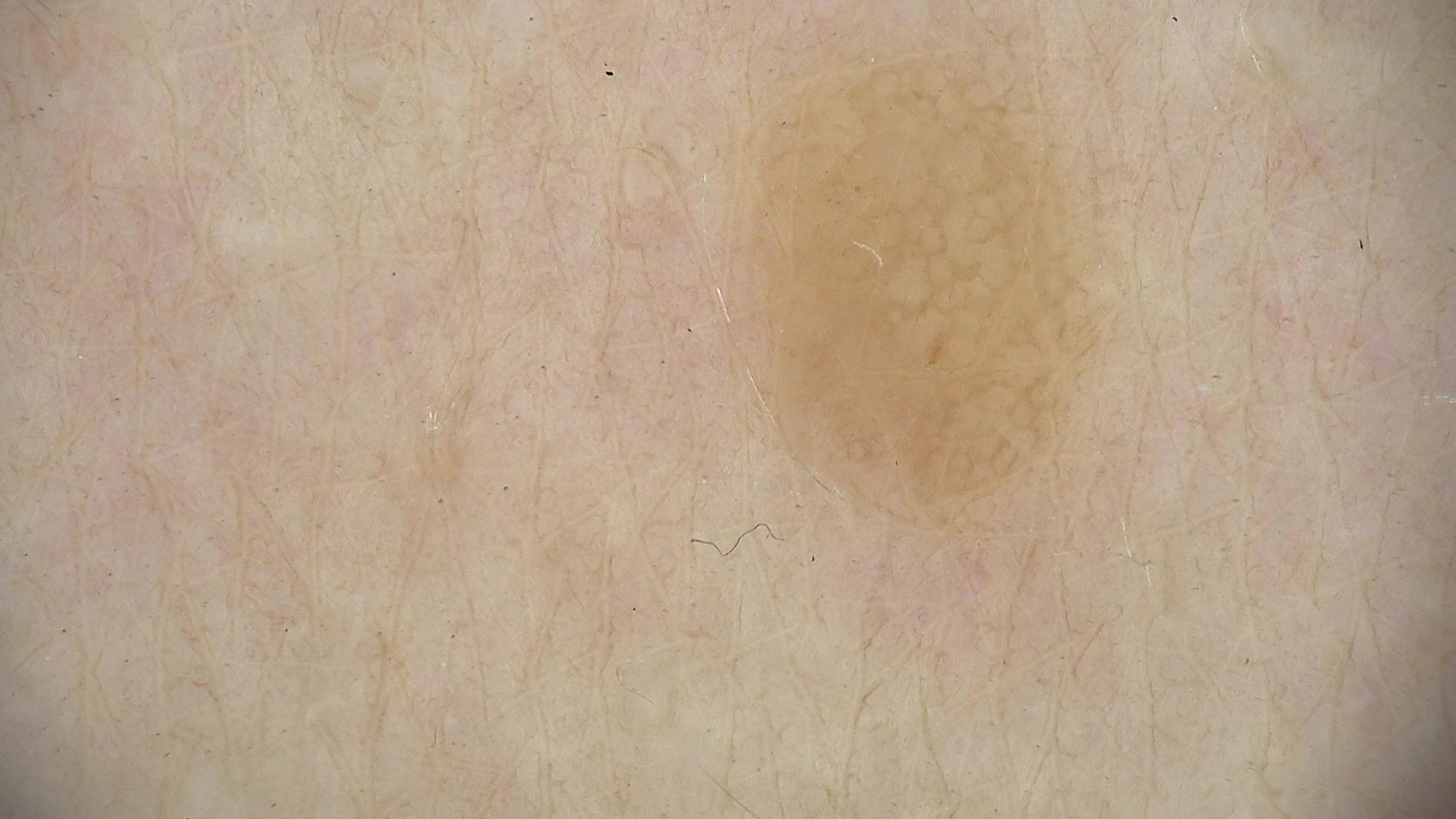image type: dermatoscopy
diagnosis: dermal nevus (expert consensus)